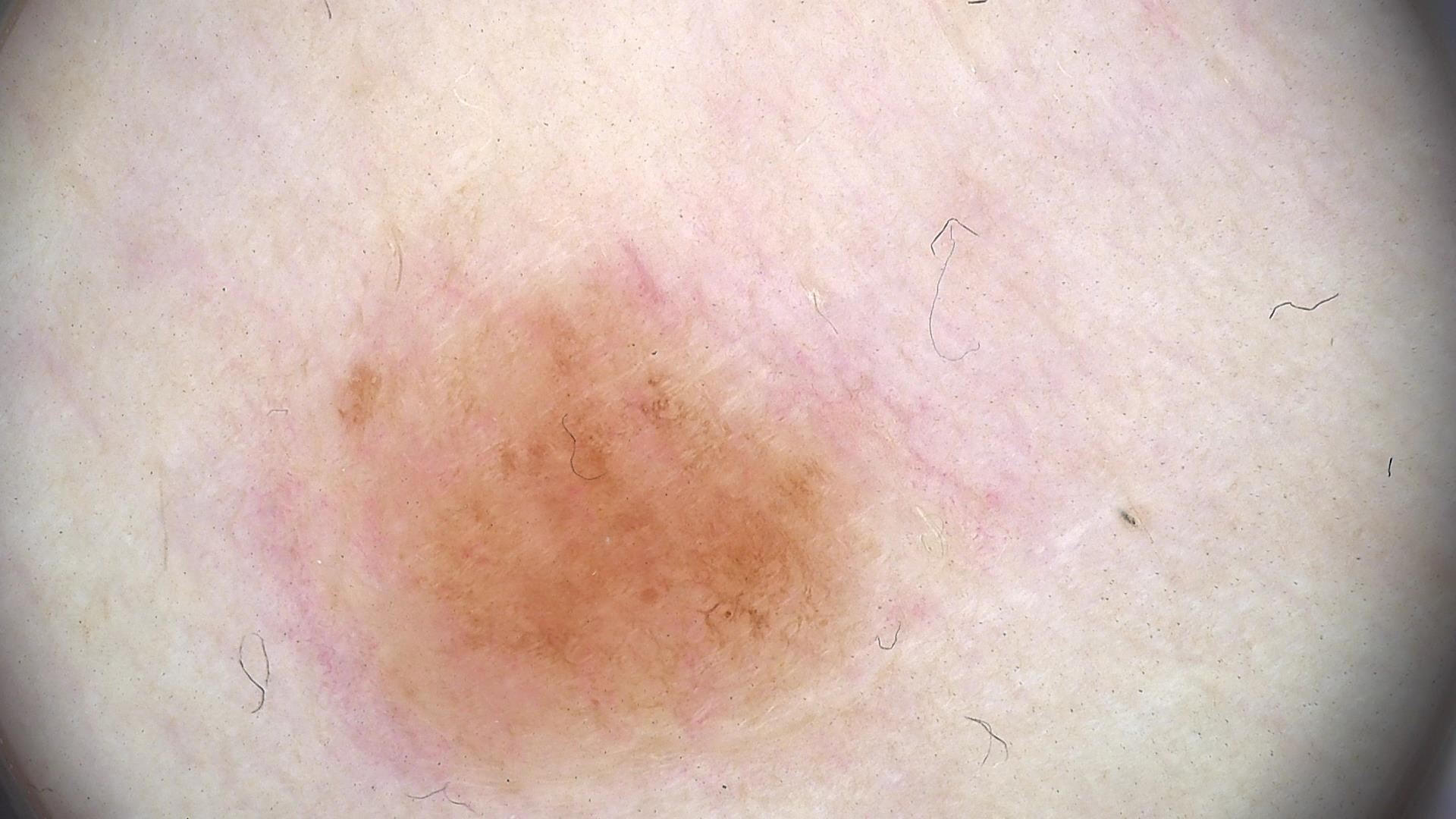Q: What is this lesion?
A: dysplastic junctional nevus (expert consensus)